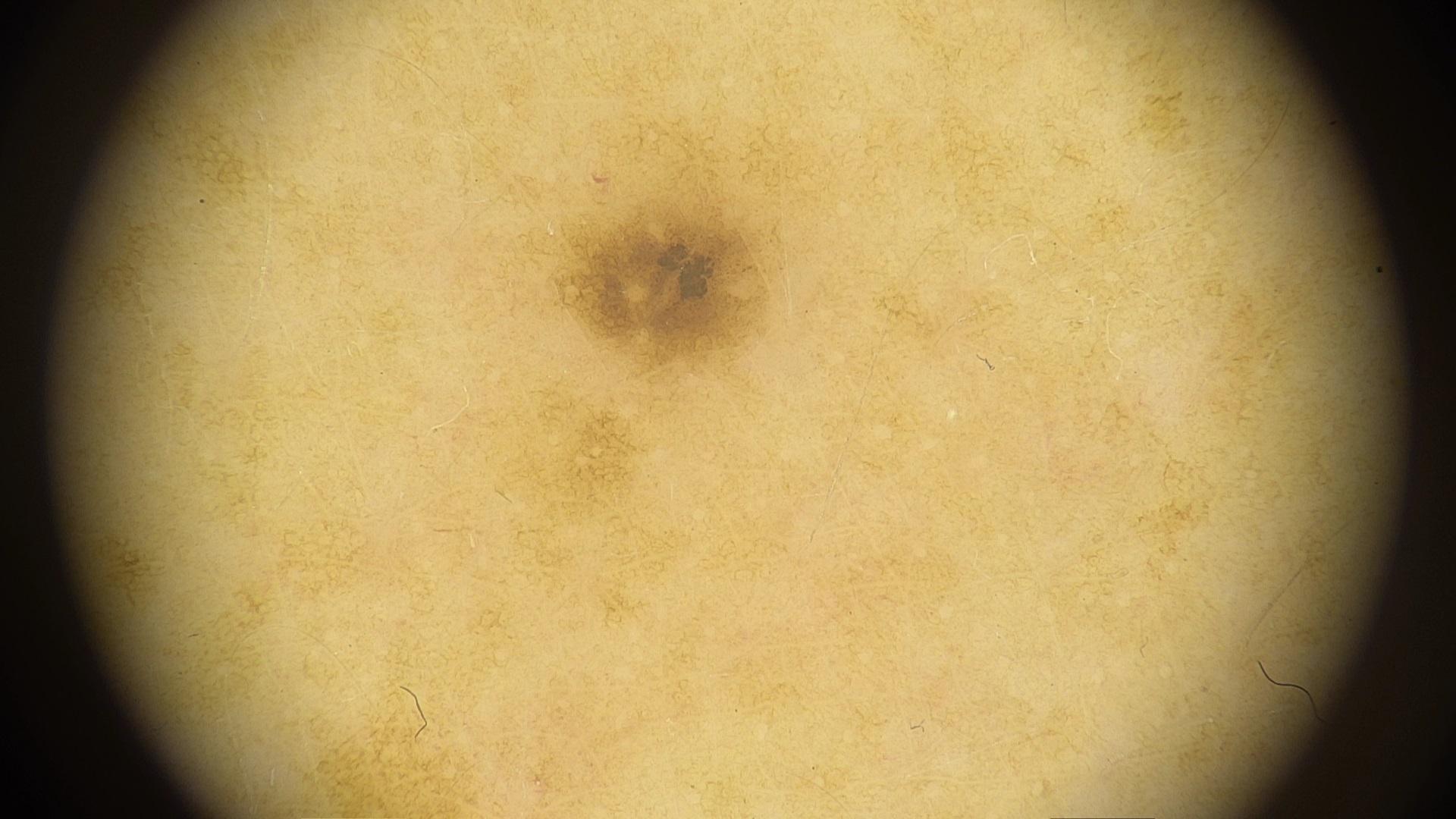Case summary: A female subject aged approximately 50. Contact-polarized dermoscopy of a skin lesion. Assessment: The clinical impression was a nevus.